The contributor reports the lesion is raised or bumpy · male patient, age 30–39 · the patient described the issue as a rash · symptoms reported: itching and bothersome appearance · the photo was captured at a distance · located on the back of the hand · present for about one day · Fitzpatrick phototype V; lay reviewers estimated 5 on the MST:
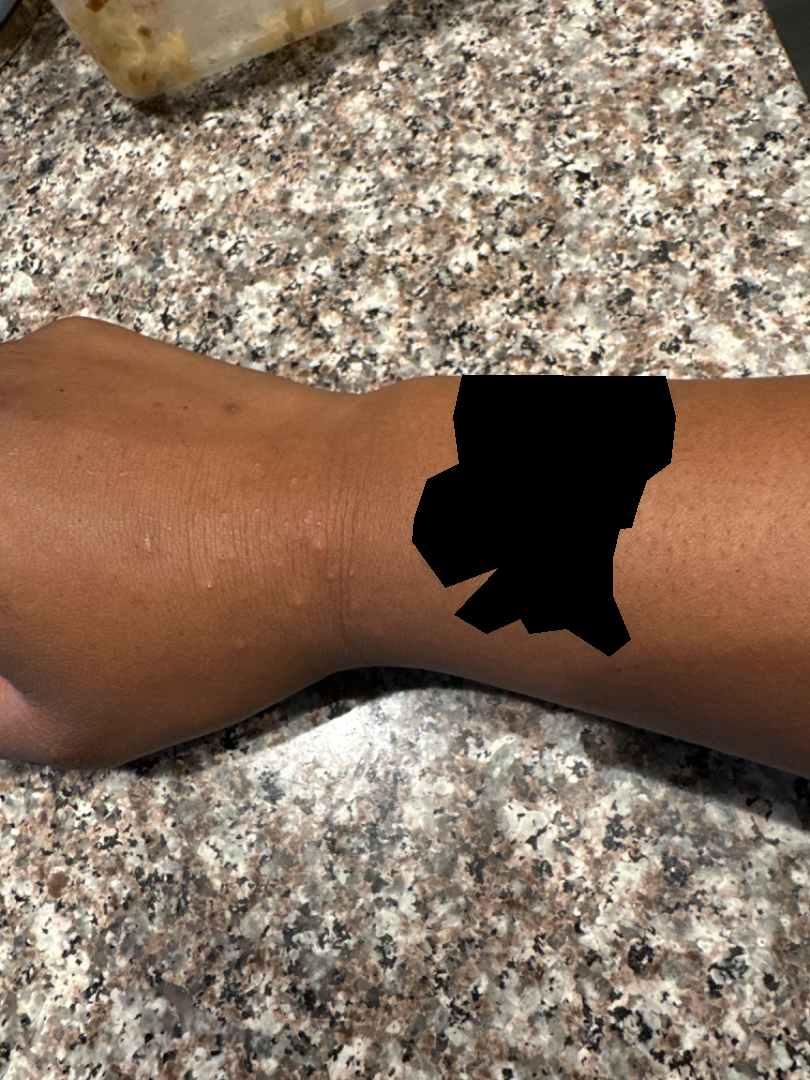diagnostic considerations=the impression on review was Folliculitis